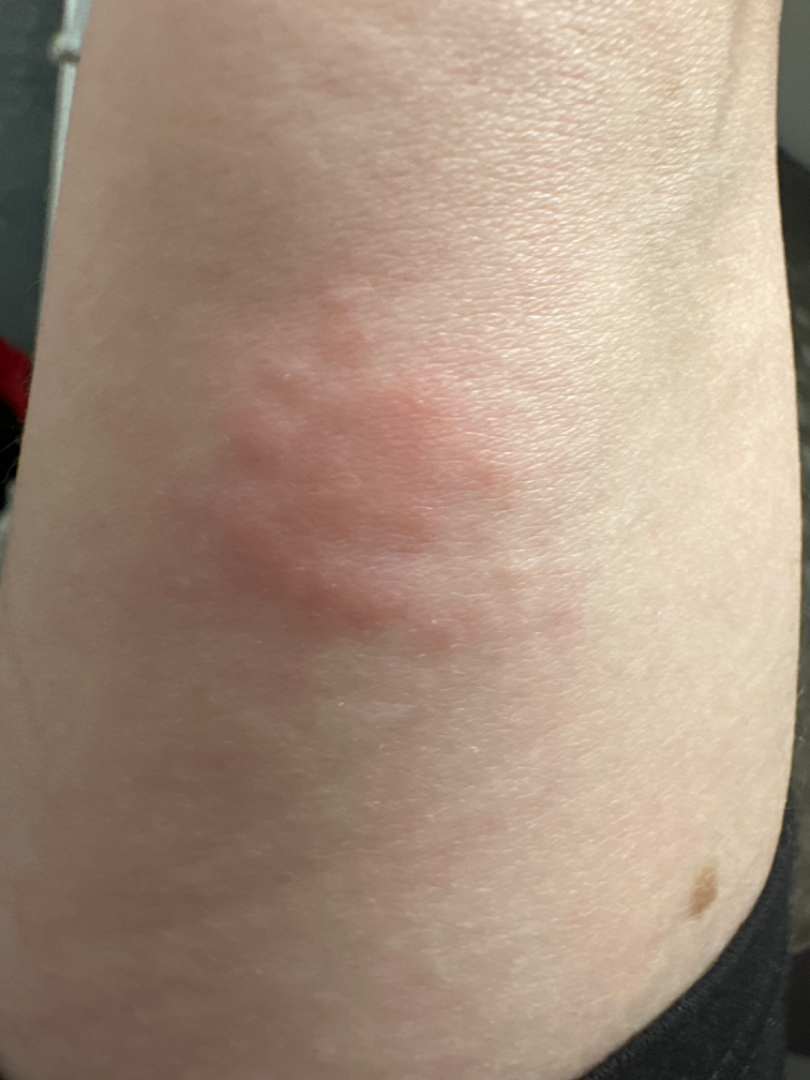symptoms: itching
body_site: arm
texture: raised or bumpy
patient_category: a rash
systemic_symptoms: none reported
shot_type: close-up
skin_tone:
  fitzpatrick: II
differential:
  Insect Bite: 0.54
  Allergic Contact Dermatitis: 0.23
  Herpes Simplex: 0.23